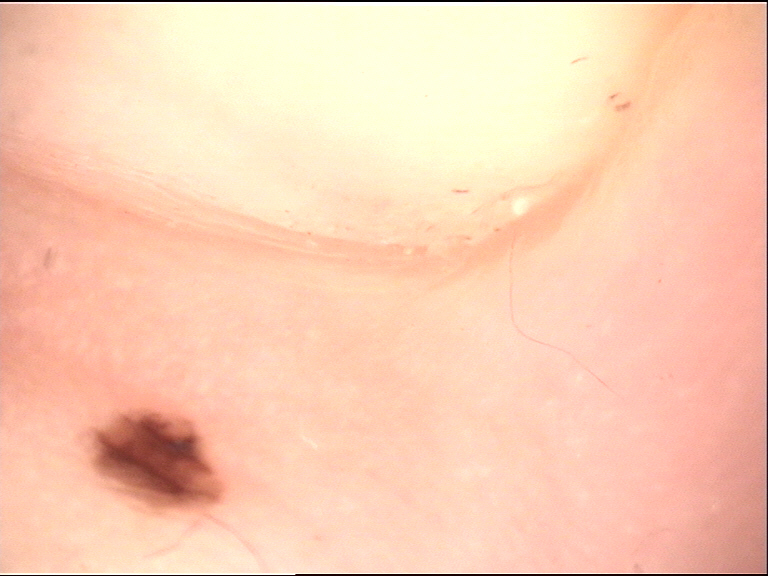A dermatoscopic image of a skin lesion. Classified as a banal lesion — an acral junctional nevus.